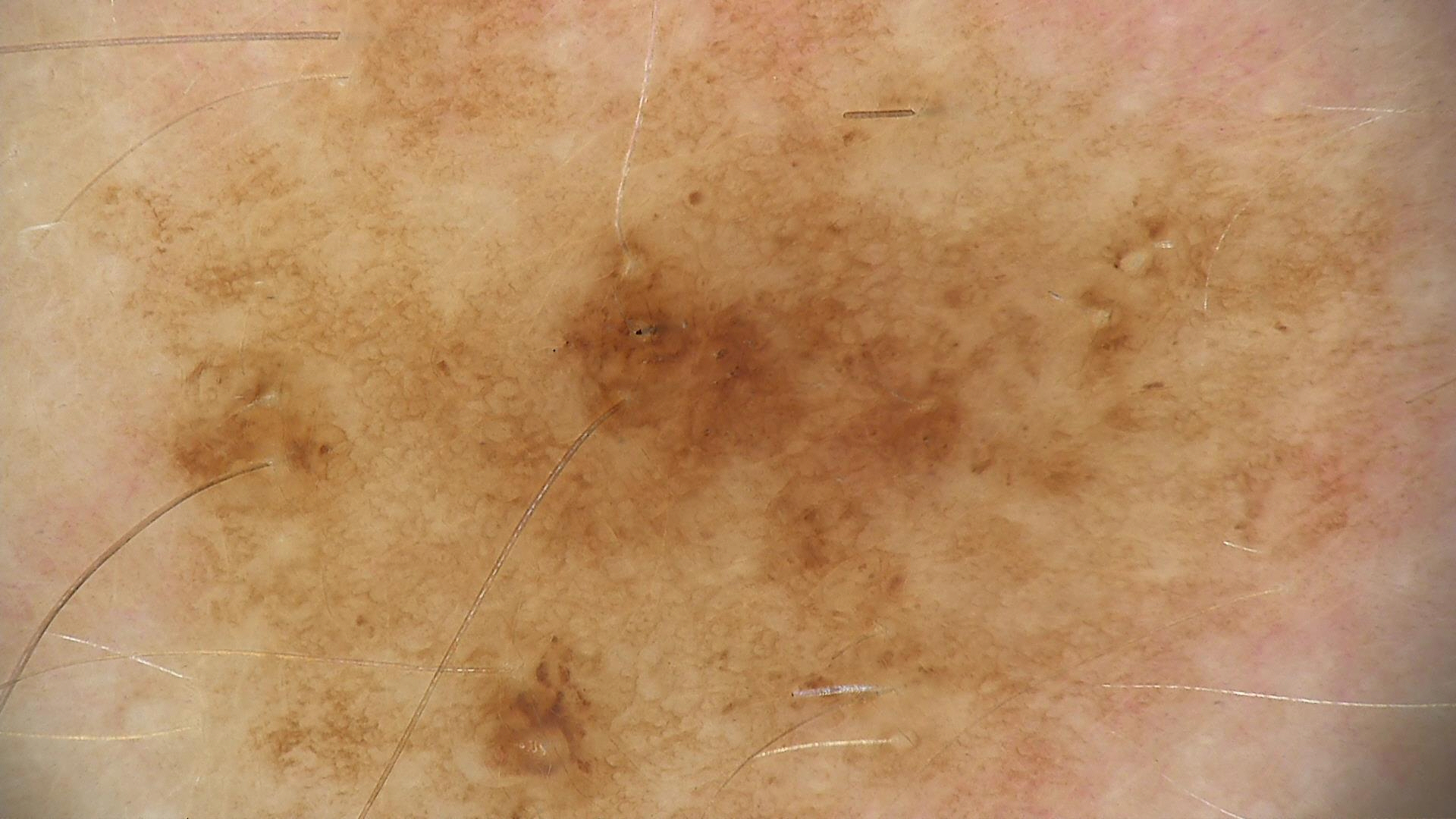A dermoscopic close-up of a skin lesion. Classified as a dysplastic junctional nevus.